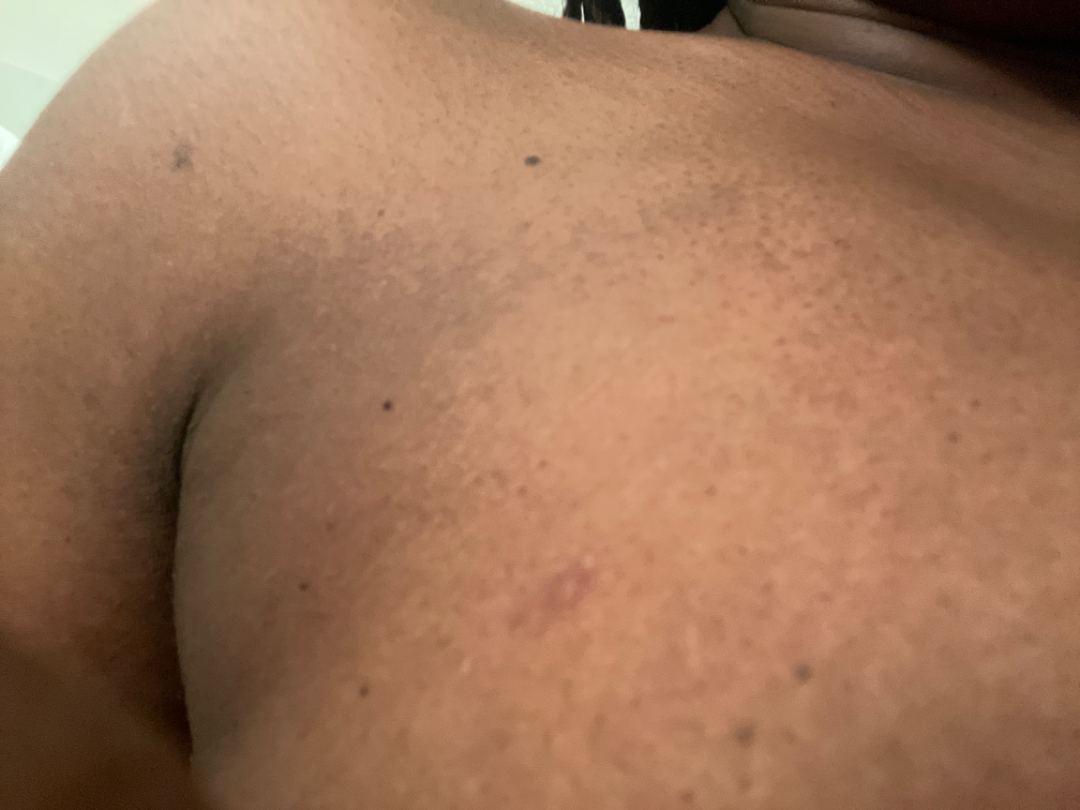Female patient, age 50–59. Close-up view. The contributor reports associated fatigue and joint pain. The lesion is associated with pain, burning and itching. The lesion is described as raised or bumpy. The patient described the issue as a rash. The affected area is the front of the torso. The condition has been present for less than one week. Tinea Versicolor and Post-Inflammatory hypopigmentation were considered with similar weight.